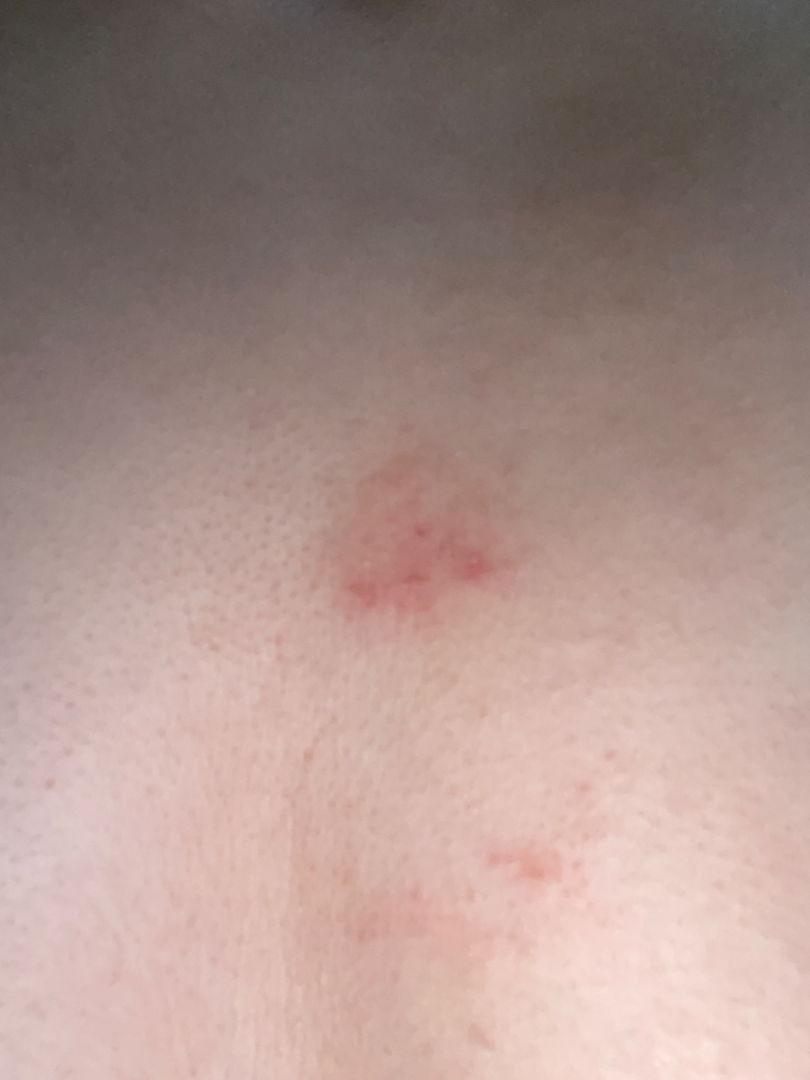site: front of the torso; framing: close-up; skin tone: lay reviewers estimated MST 2; described texture: rough or flaky; reported symptoms: bleeding, itching, pain and bothersome appearance; contributor: female, age 18–29; clinical impression: the differential is split between Eczema and Herpes Simplex.